A dermoscopy image of a single skin lesion.
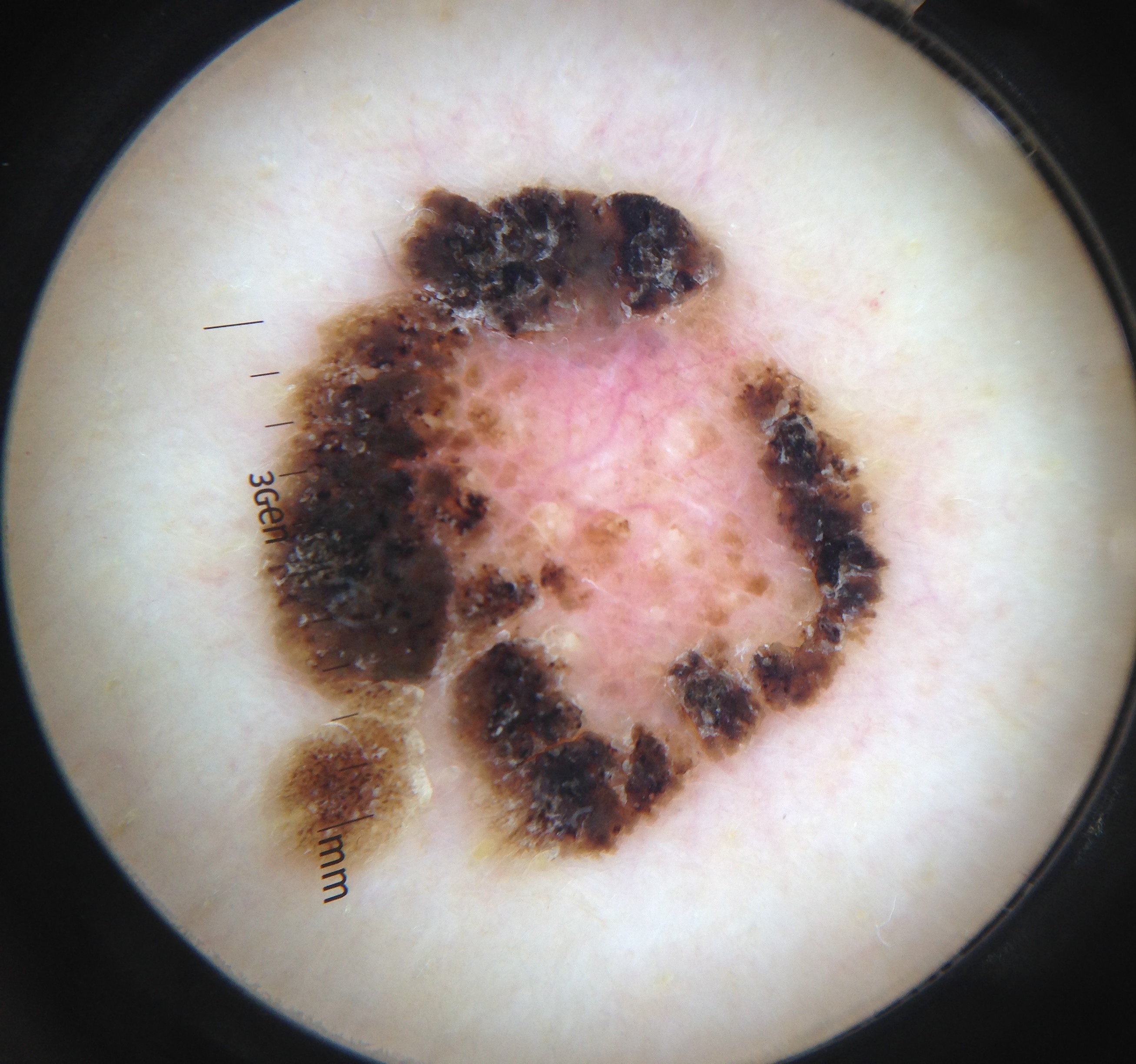Case:
* subtype — keratinocytic
* class — seborrheic keratosis (expert consensus)